A dermoscopy image of a single skin lesion: 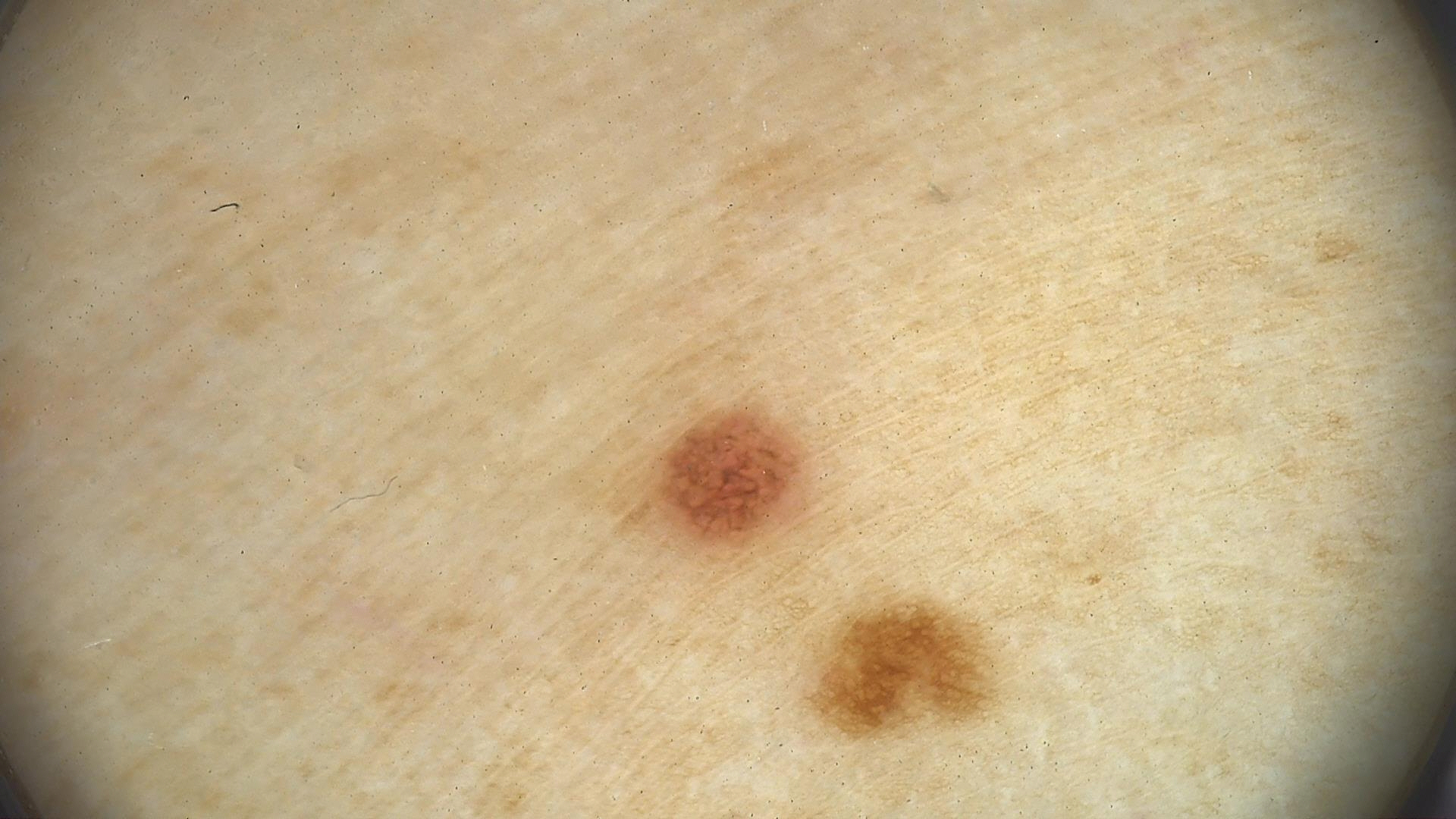{"diagnosis": {"name": "dysplastic junctional nevus", "code": "jd", "malignancy": "benign", "super_class": "melanocytic", "confirmation": "expert consensus"}}